A female patient 55 years old · by history, no tobacco use and no alcohol use · the patient is Fitzpatrick skin type III · a clinical close-up photograph of a skin lesion:
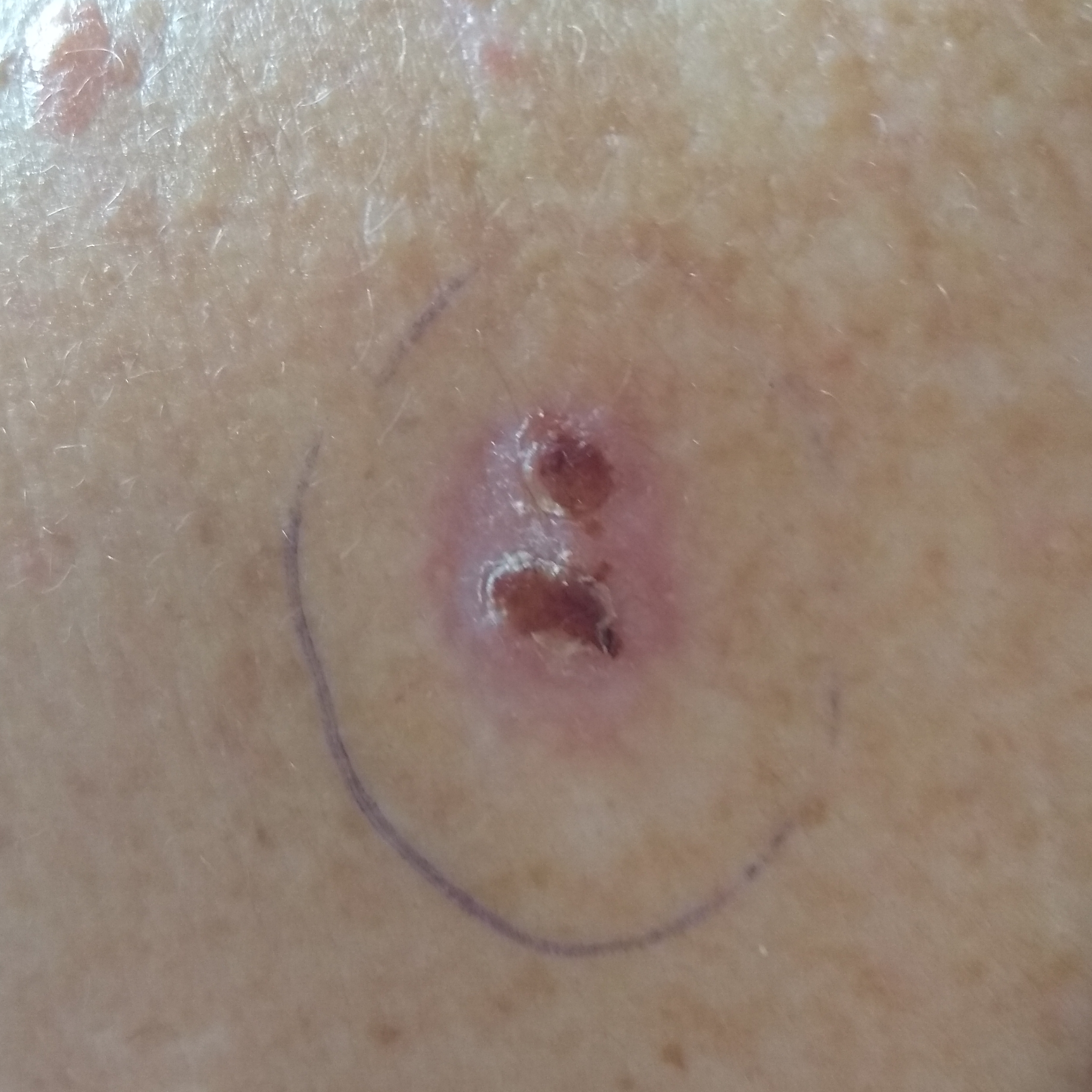The lesion involves the back.
Measuring about 16 × 13 mm.
The patient describes that the lesion itches, is elevated, has grown, and has bled, but has not changed.
Biopsy-confirmed as a skin cancer — a basal cell carcinoma.